Dermoscopy of a skin lesion:
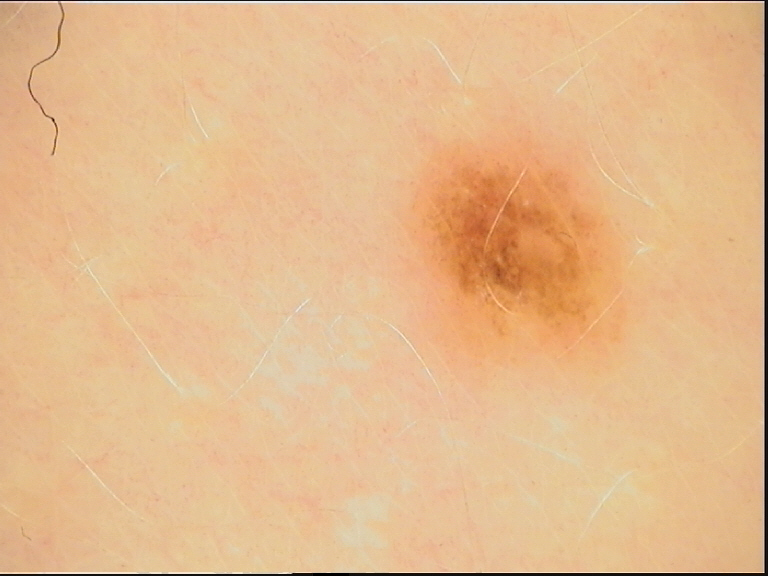<lesion>
  <diagnosis>
    <name>junctional nevus</name>
    <code>jb</code>
    <malignancy>benign</malignancy>
    <super_class>melanocytic</super_class>
    <confirmation>expert consensus</confirmation>
  </diagnosis>
</lesion>